A dermoscopic close-up of a skin lesion. A male patient, aged 83 or over.
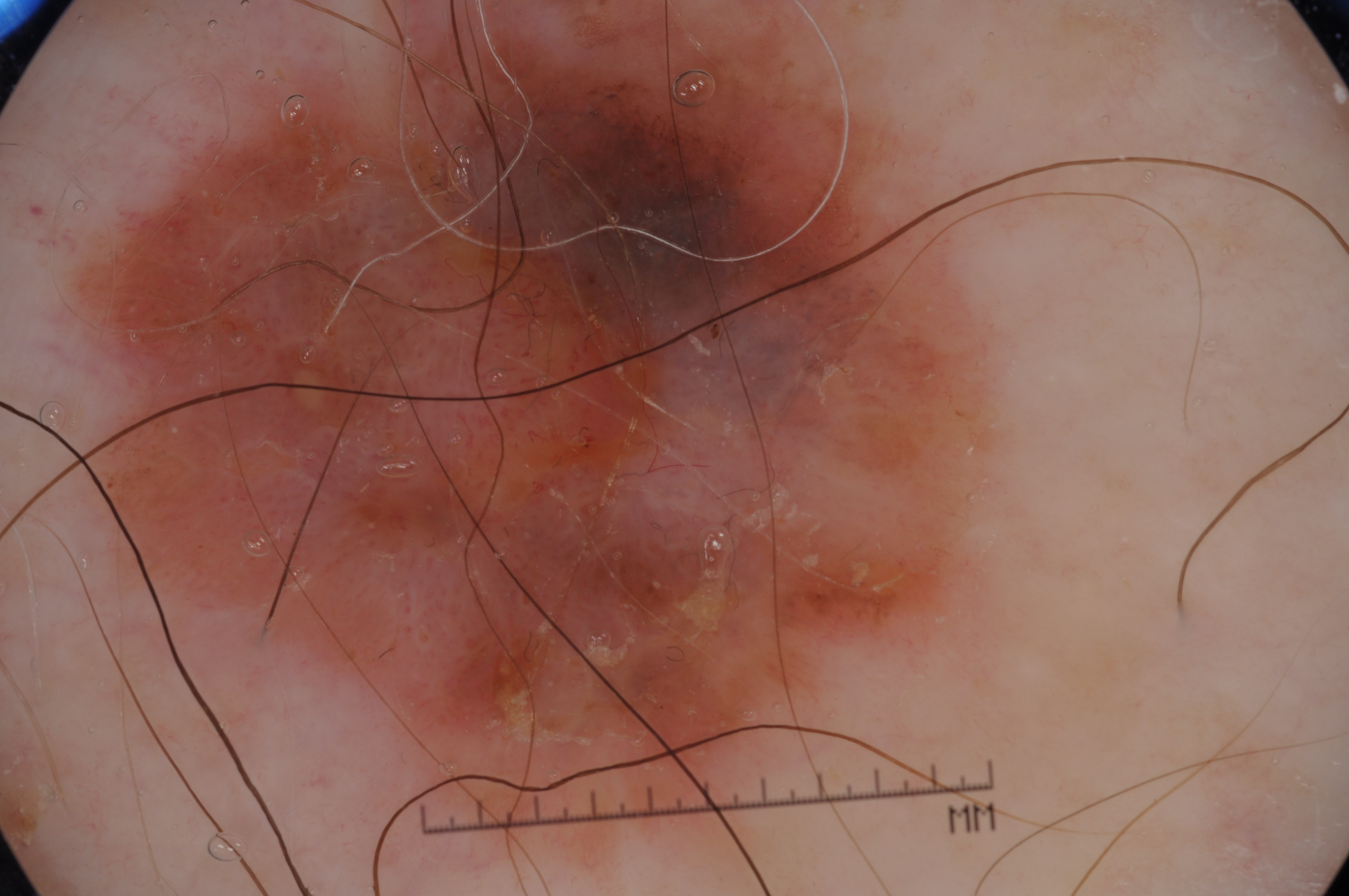Image and clinical context:
The lesion is bounded by [74, 0, 1012, 861]. The lesion reaches the border of the frame. The lesion covers approximately 51% of the dermoscopic field. Dermoscopic assessment notes negative network and pigment network, with no milia-like cysts or streaks.
Diagnosis:
Biopsy-confirmed as a melanoma, a malignancy.